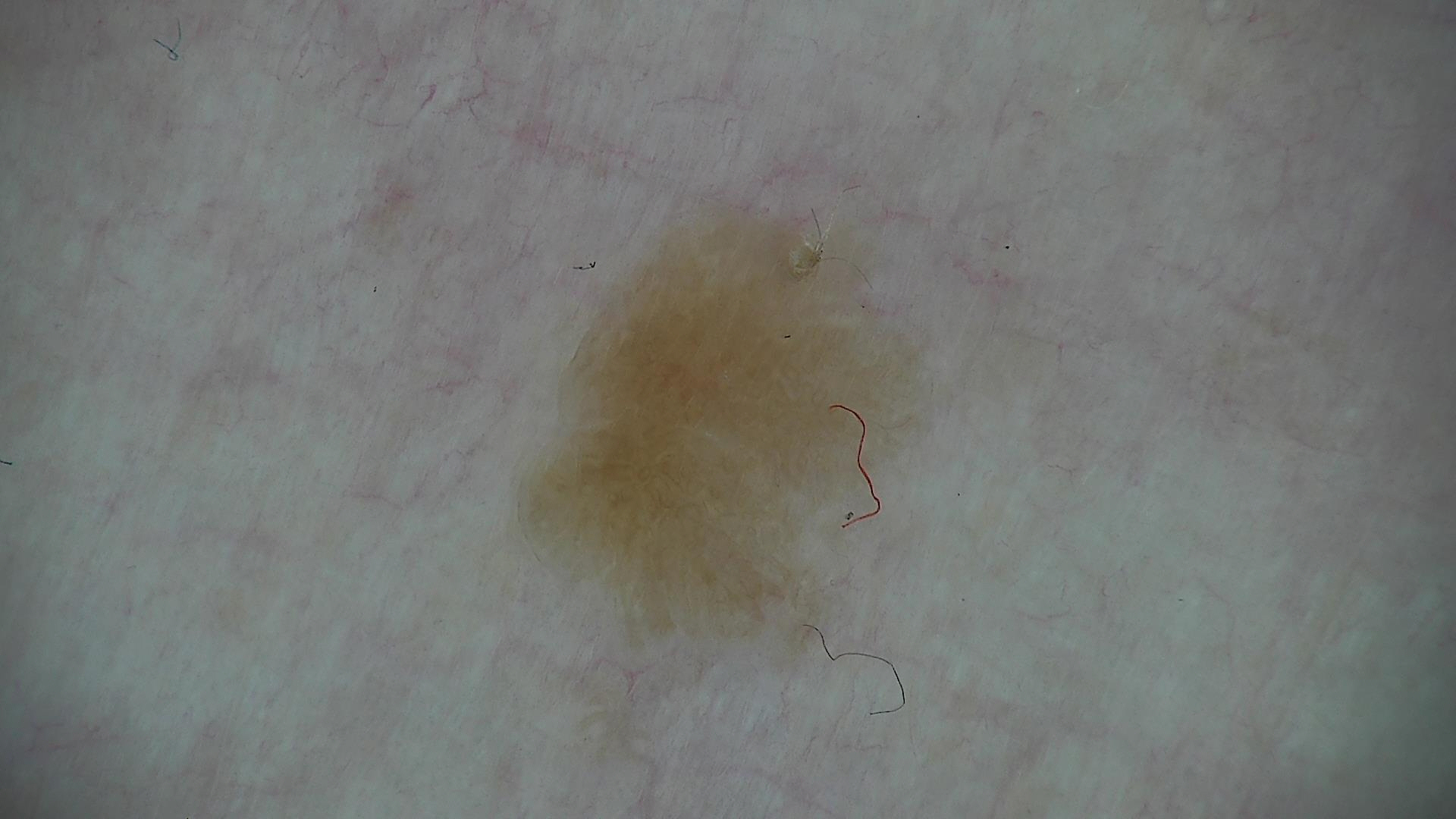Dermoscopy of a skin lesion. The morphology is that of a keratinocytic lesion. Labeled as a benign lesion — a seborrheic keratosis.